A dermoscopic photograph of a skin lesion.
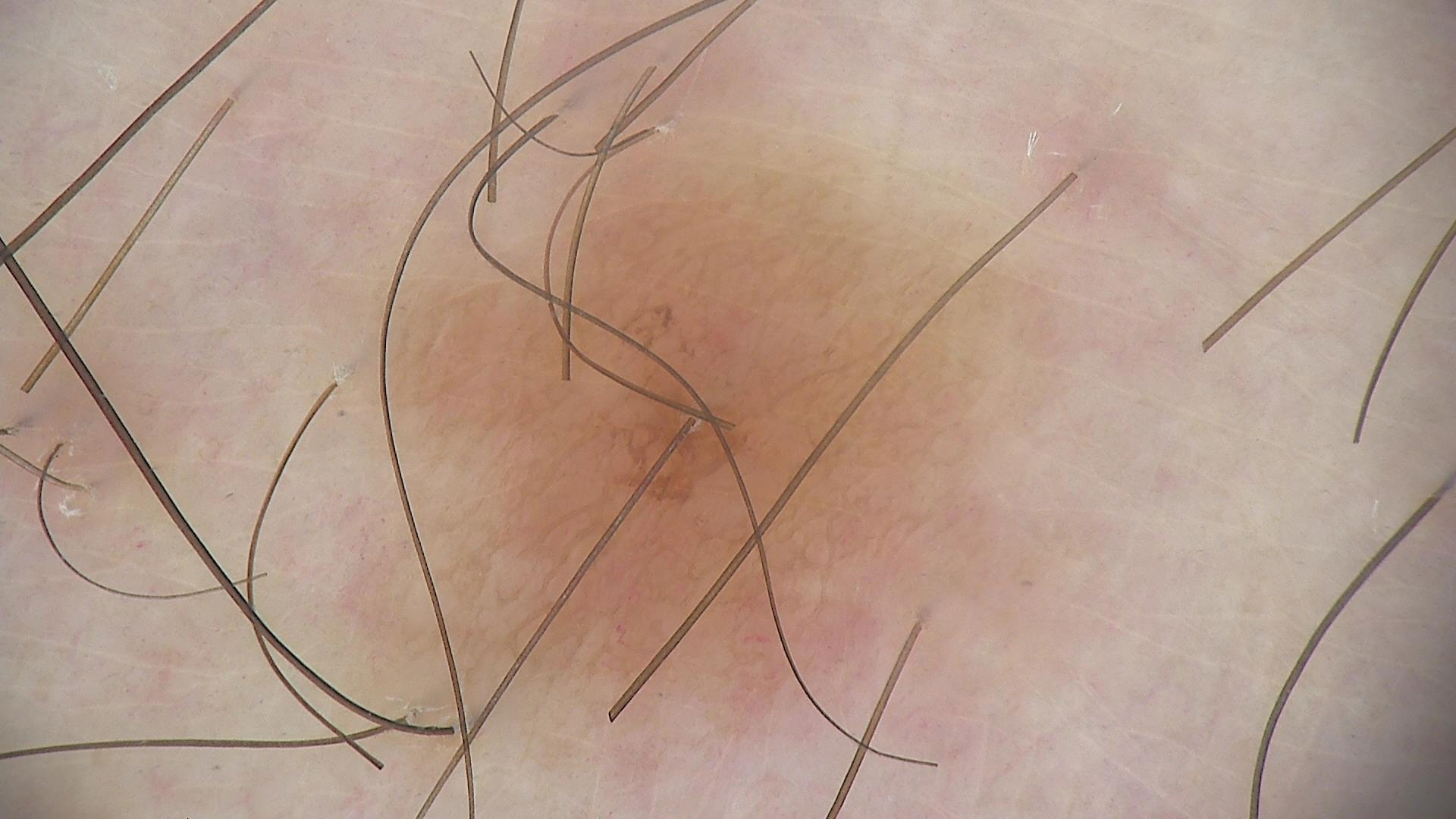The diagnosis was a dysplastic junctional nevus.